A dermoscopic image of a skin lesion:
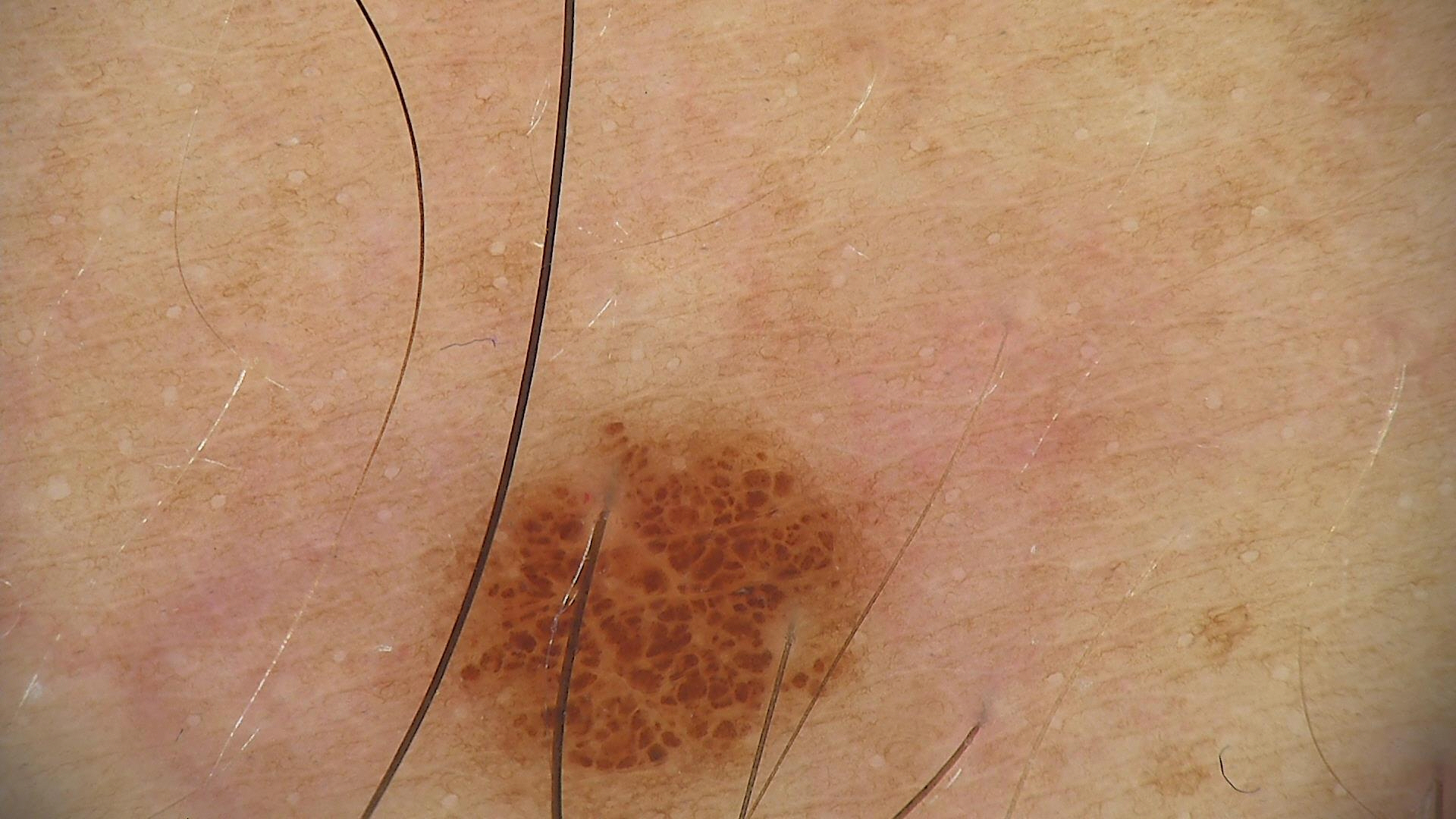Impression: Diagnosed as a benign lesion — a dysplastic junctional nevus.